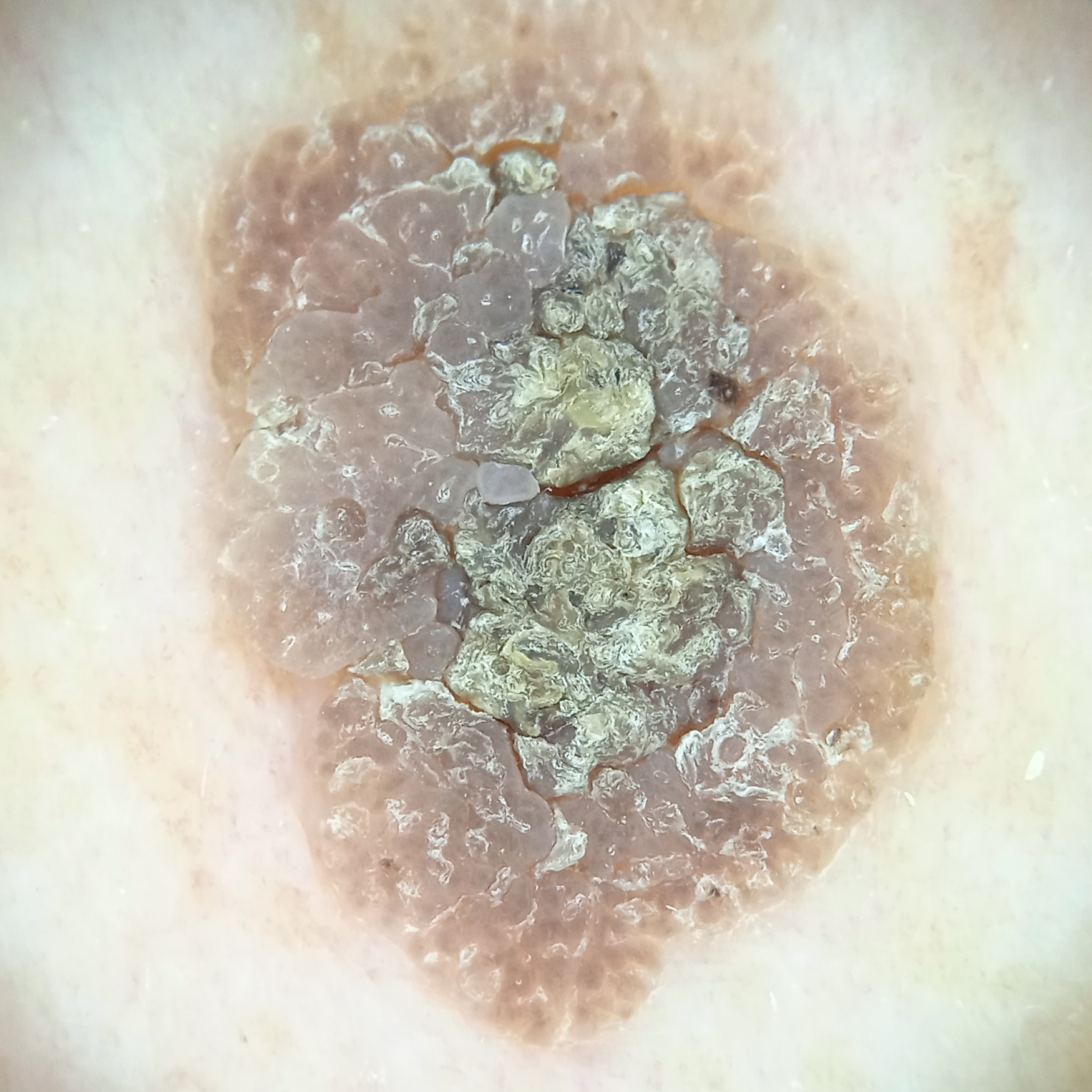Findings:
A skin lesion imaged with a dermatoscope. A male subject 62 years of age. Acquired for a research image collection, with no referral diagnosis. Few moles overall by the patient's own estimate. The lesion involves the back. Measuring roughly 10.9 mm.
Conclusion:
The consensus diagnosis for this lesion was a seborrheic keratosis.